A dermoscopic photograph of a skin lesion: 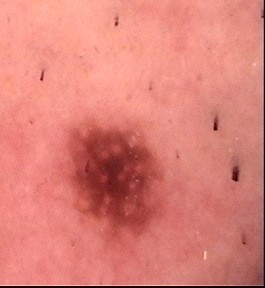classification: banal, compound; diagnostic label: Miescher nevus (expert consensus).